A dermatoscopic image of a skin lesion:
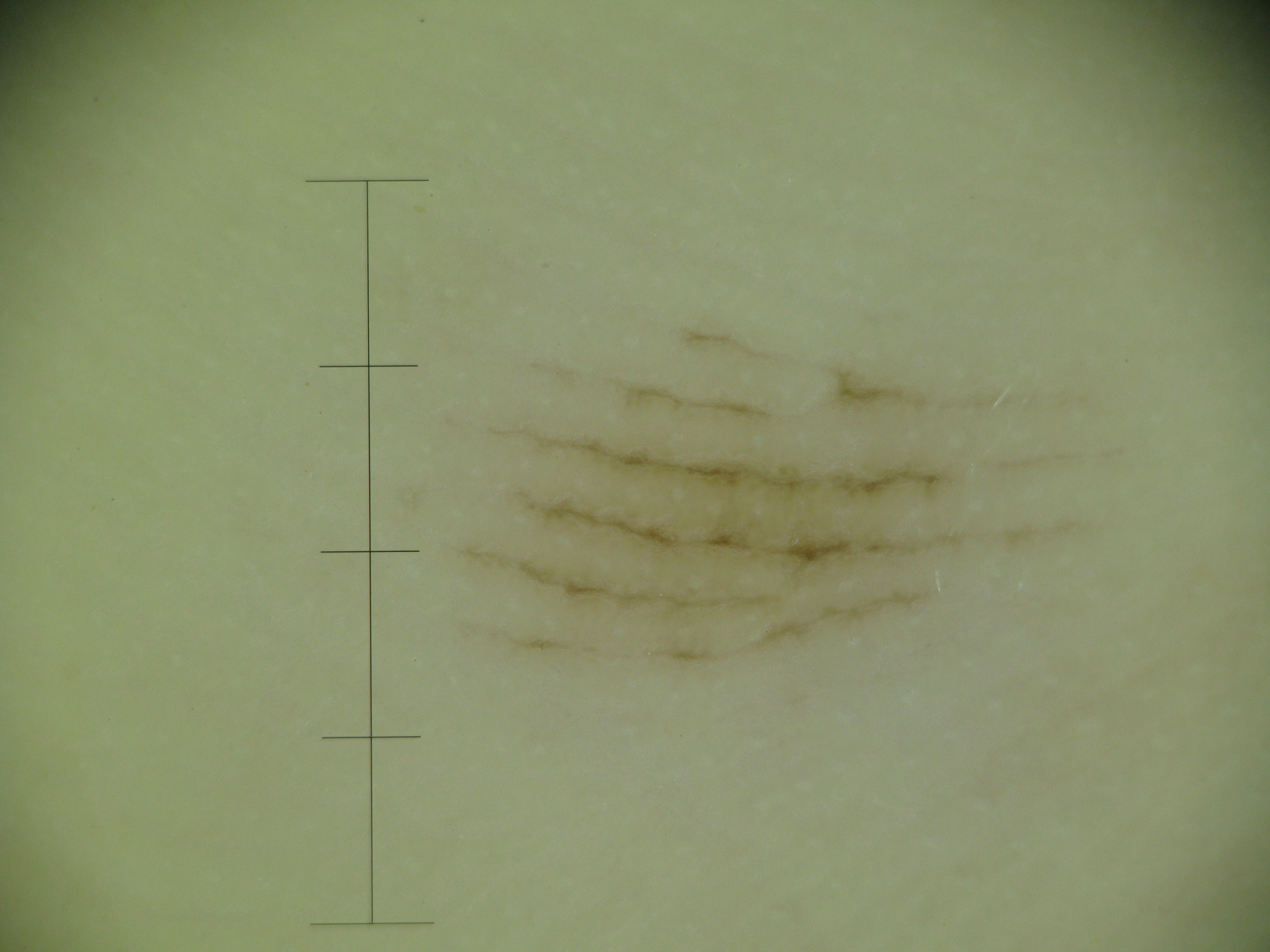Case:
– subtype · banal
– diagnostic label · acral junctional nevus (expert consensus)